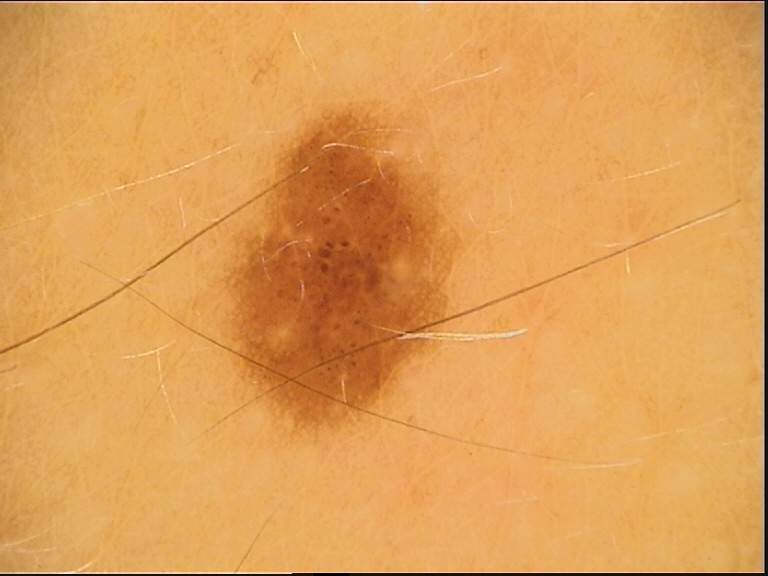{"diagnosis": {"name": "dysplastic junctional nevus", "code": "jd", "malignancy": "benign", "super_class": "melanocytic", "confirmation": "expert consensus"}}